A dermoscopy image of a single skin lesion.
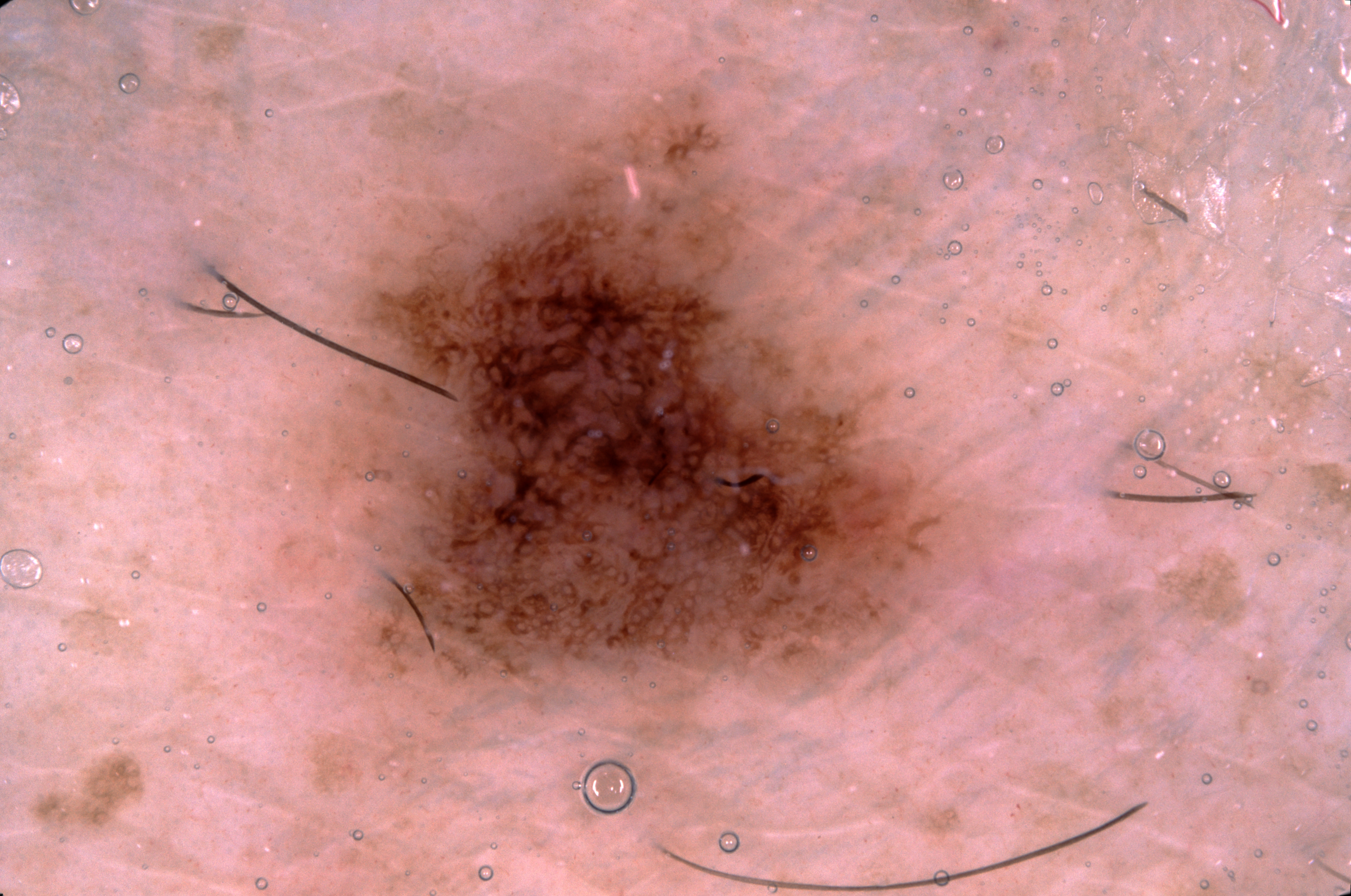Summary:
As (left, top, right, bottom), the lesion occupies the region [175,78,987,747]. The dermoscopic pattern shows pigment network. A mid-sized lesion within the field.
Assessment:
The clinical diagnosis was a melanocytic nevus.